A skin lesion imaged with a dermatoscope: 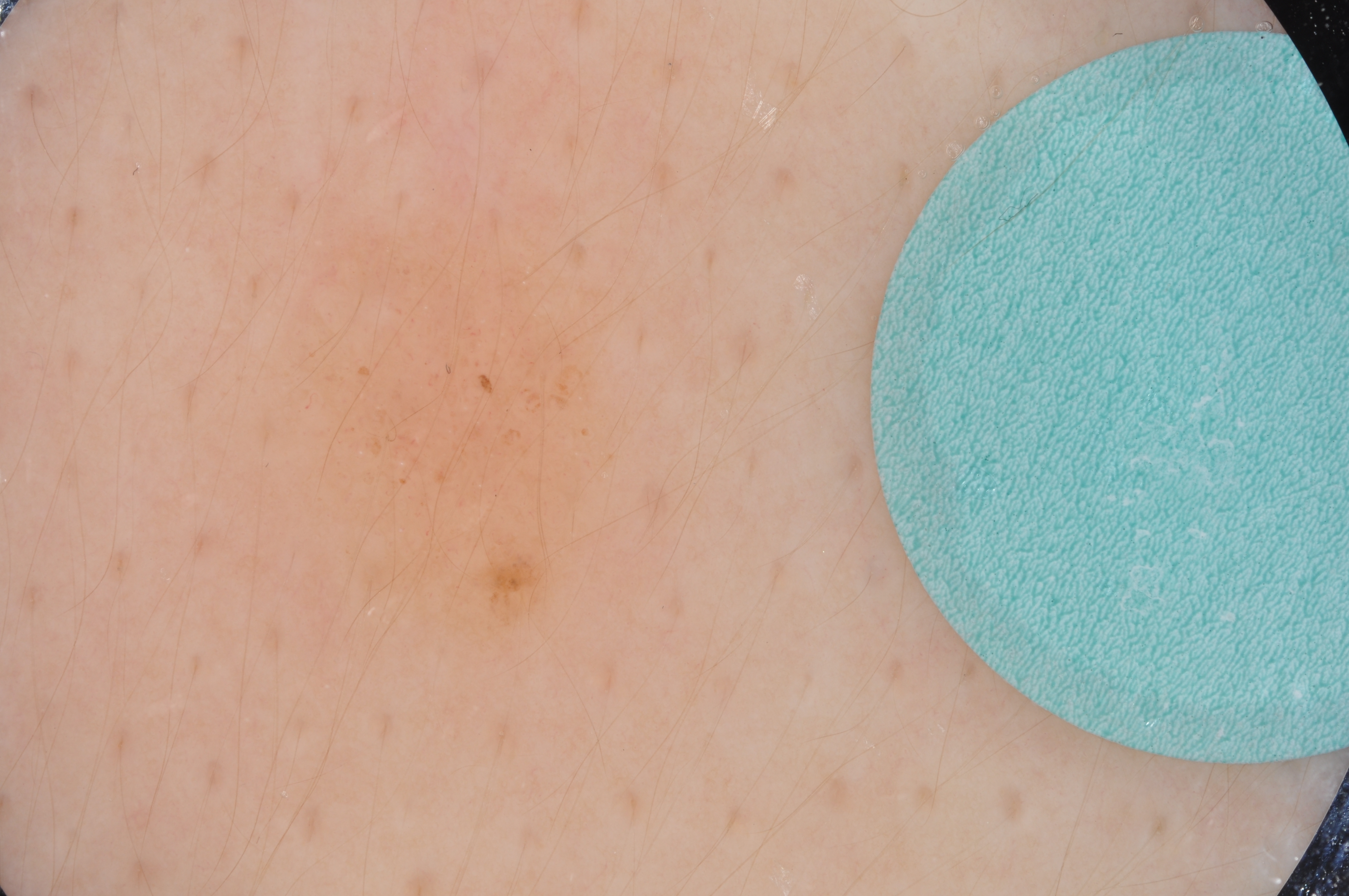Case summary: The lesion takes up about 11% of the image. Dermoscopic examination shows no streaks or globules. The lesion's extent is x1=245 y1=207 x2=629 y2=654. Impression: The clinical diagnosis was a benign skin lesion.